The patient did not report lesion symptoms. The patient notes the lesion is raised or bumpy. No associated systemic symptoms reported. This is a close-up image. The condition has been present for more than one year. The back of the torso, front of the torso and arm are involved. Skin tone: Fitzpatrick II.
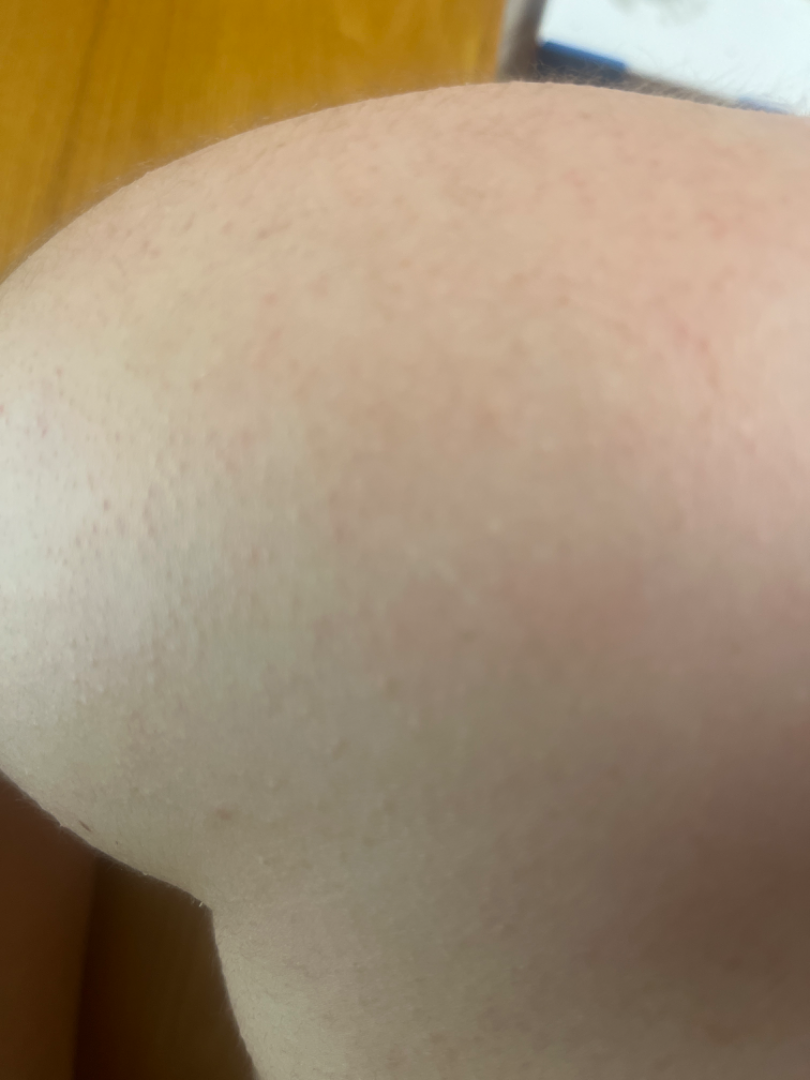{
  "differential": {
    "Keratosis pilaris": 0.67,
    "Allergic Contact Dermatitis": 0.33
  }
}